The condition has been present for less than one week. An image taken at an angle. The arm is involved. The contributor notes the lesion is raised or bumpy. The patient described the issue as a rash. The contributor notes enlargement and itching:
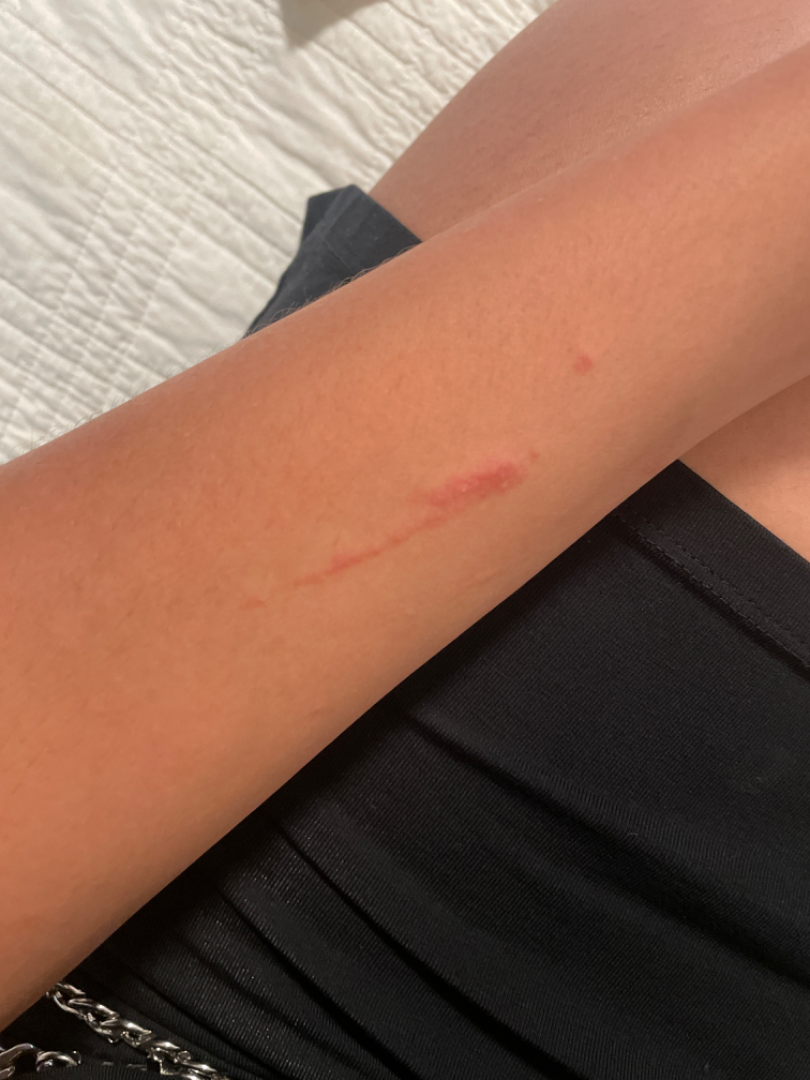Findings:
On photographic review: most likely Allergic Contact Dermatitis; also raised was Contact dermatitis.